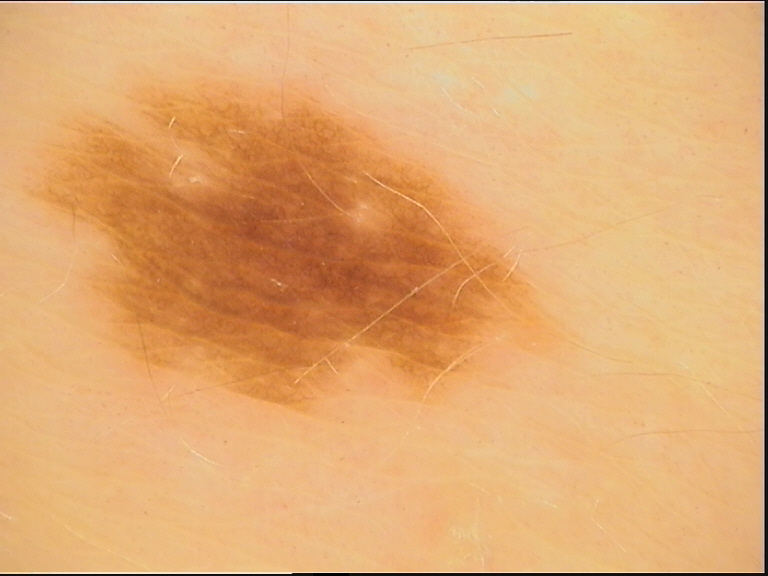A dermatoscopic image of a skin lesion. The diagnostic label was a benign lesion — a dysplastic junctional nevus.